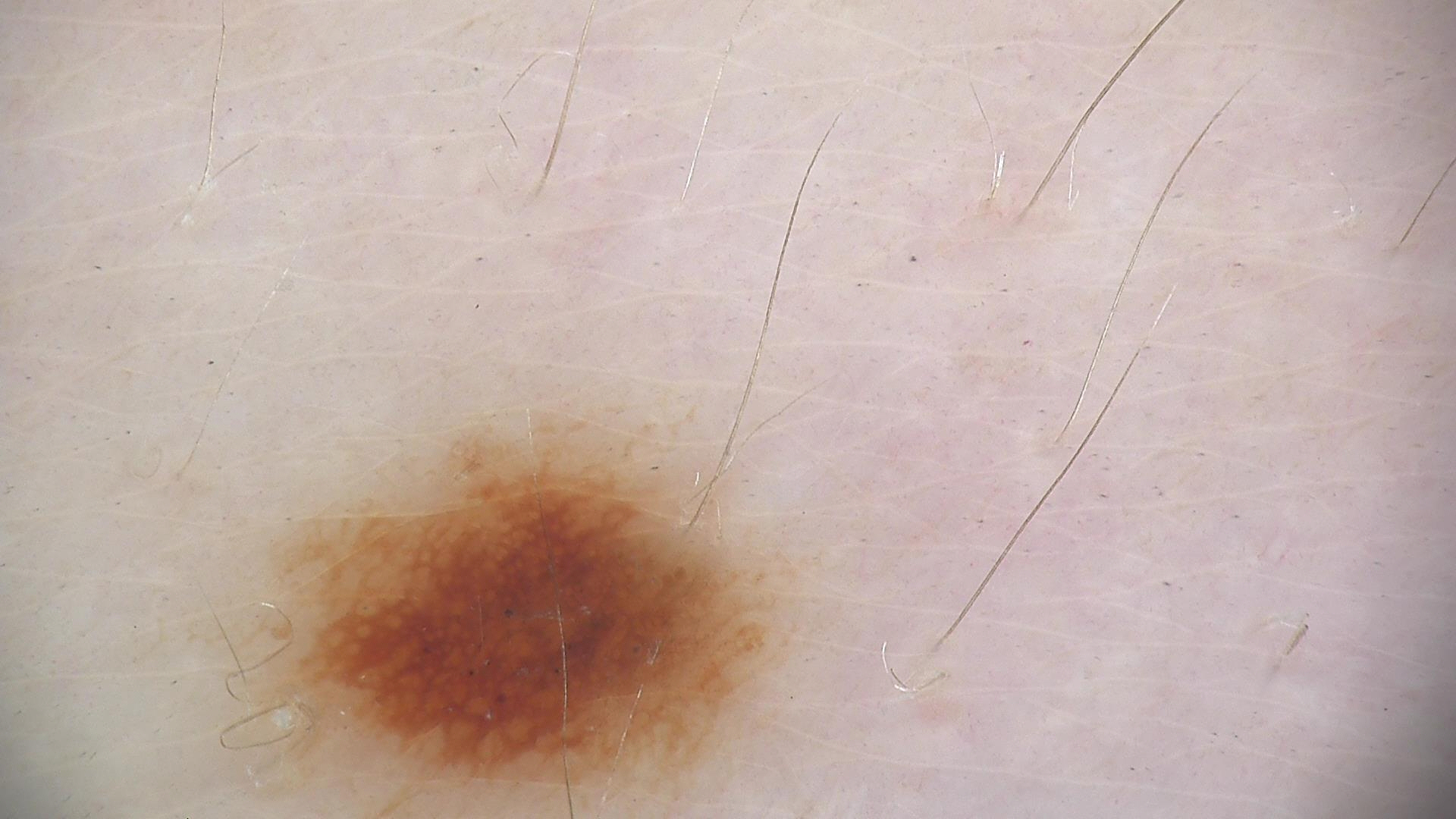Case:
- image — dermoscopy
- assessment — dysplastic junctional nevus (expert consensus)